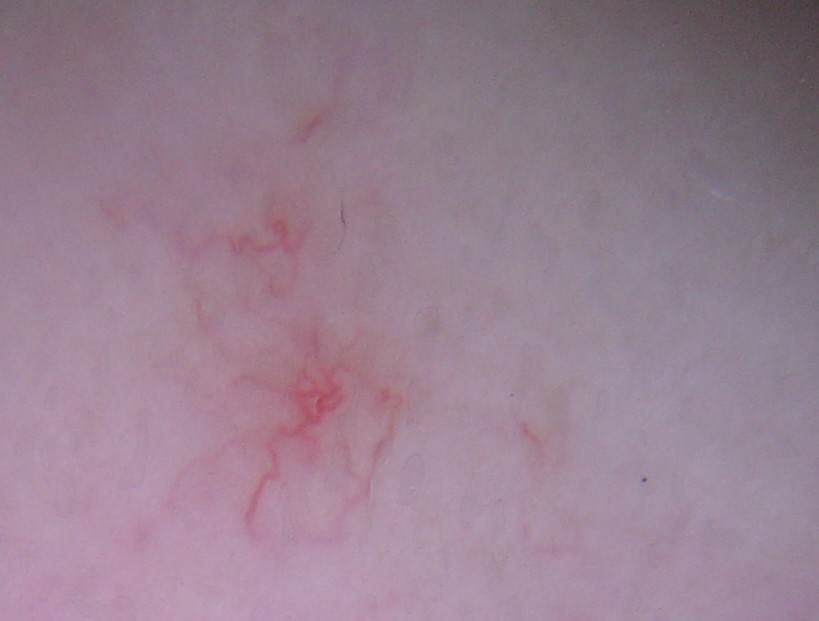imaging — dermatoscopy; lesion type — vascular; diagnostic label — spider angioma (expert consensus).